The lesion involves the leg, a close-up photograph.
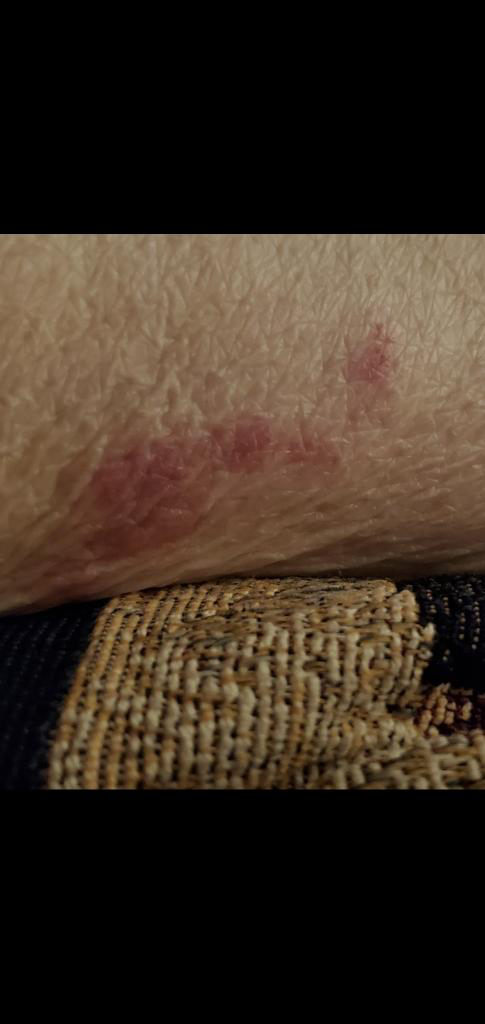Reviewed remotely by one dermatologist: most consistent with ecchymoses.